Dermoscopy of a skin lesion:
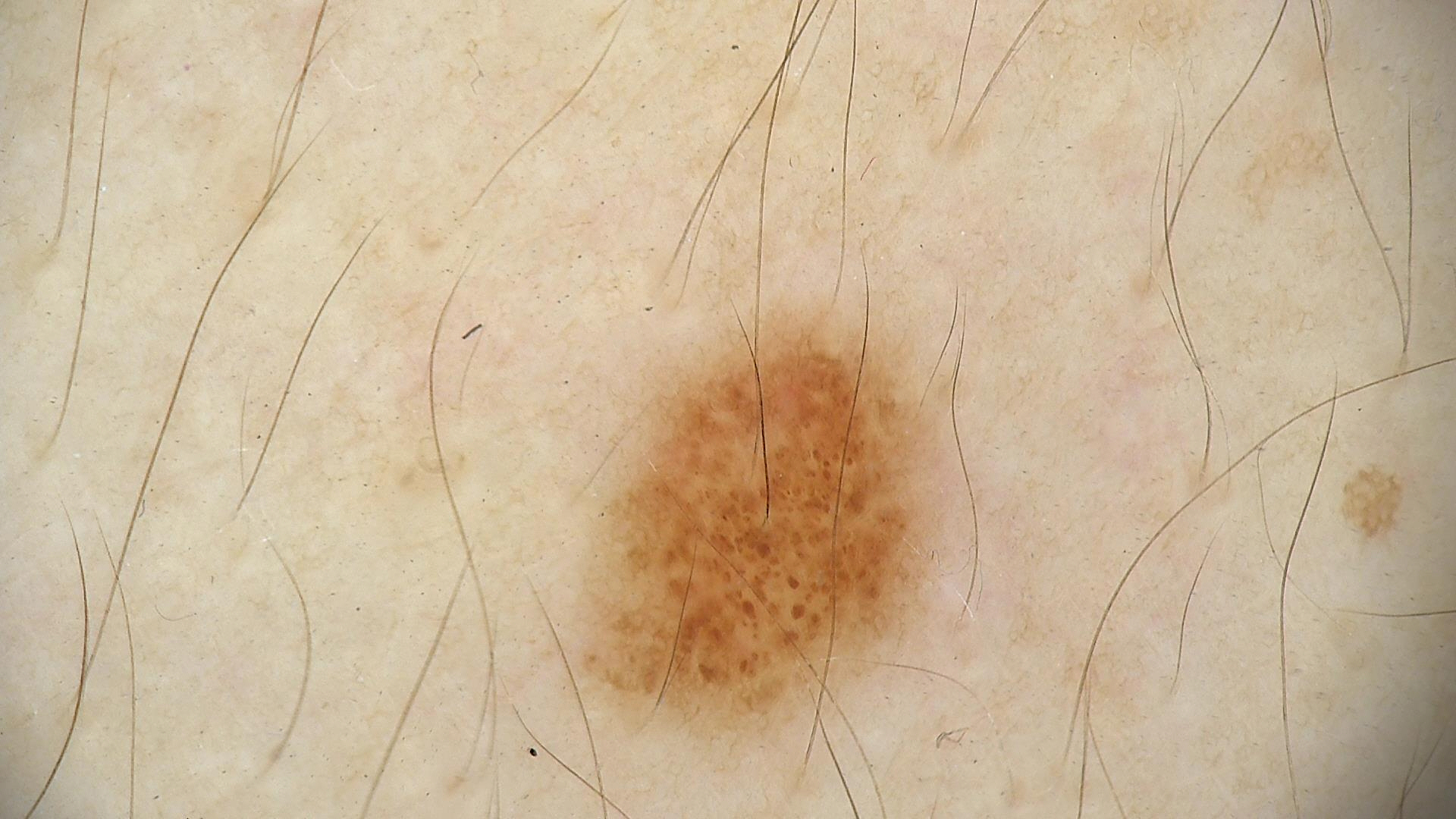Case:
– diagnosis — dysplastic junctional nevus (expert consensus)